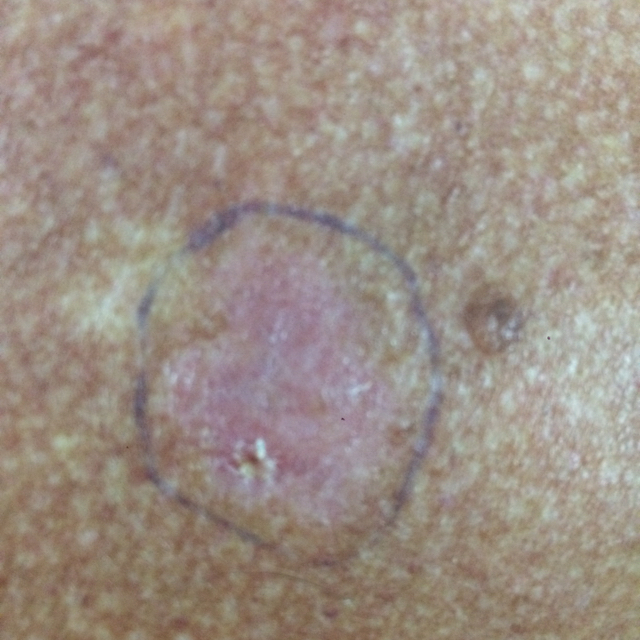image type = clinical photo | subject = 55 years of age | location = the back | reported symptoms = itching / no pain, no bleeding | impression = actinic keratosis (clinical consensus).